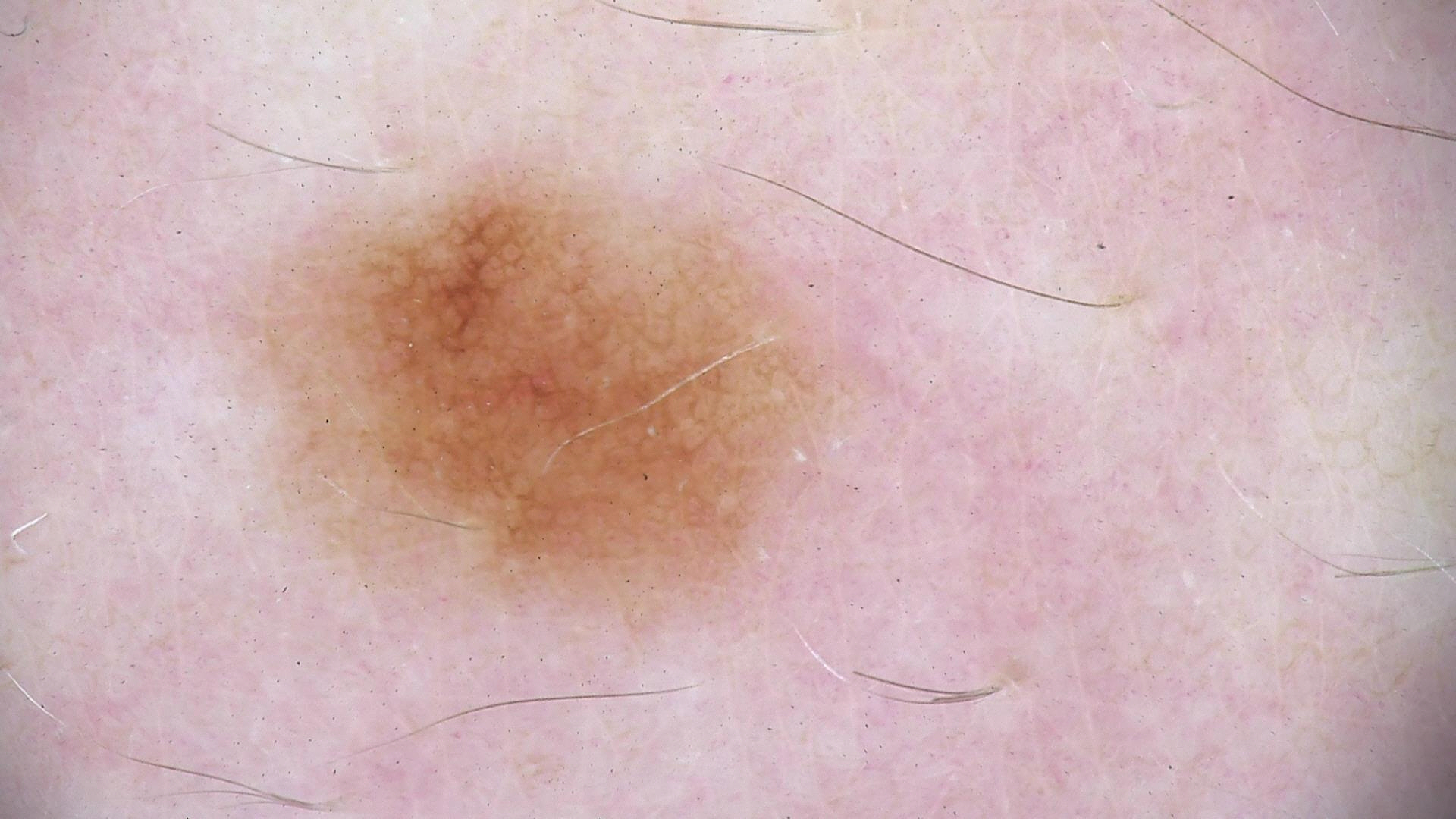modality = dermoscopy
class = dysplastic junctional nevus (expert consensus)